The lesion involves the arm · female patient, age 50–59 · this image was taken at a distance: 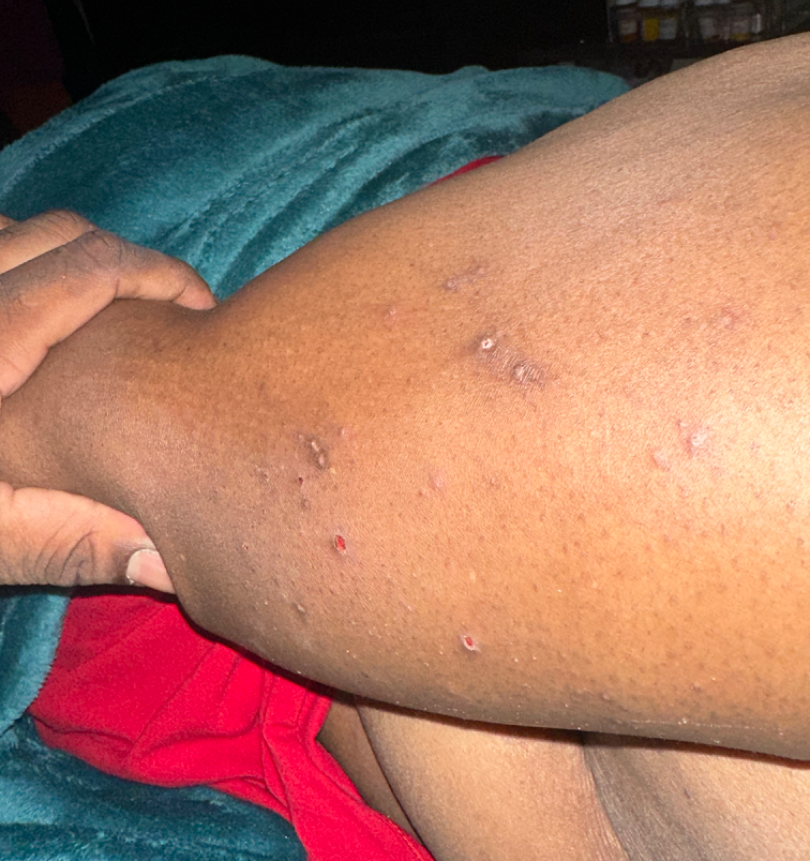dermatologist impression — Prurigo nodularis (weight 0.67); Eczema (weight 0.33)